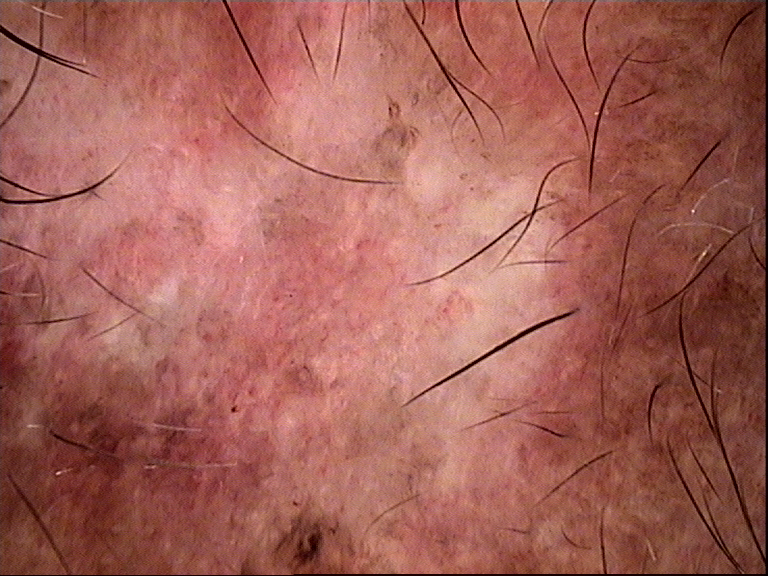A dermatoscopic image of a skin lesion.
This is a keratinocytic lesion.
Histopathologically confirmed as a basal cell carcinoma.